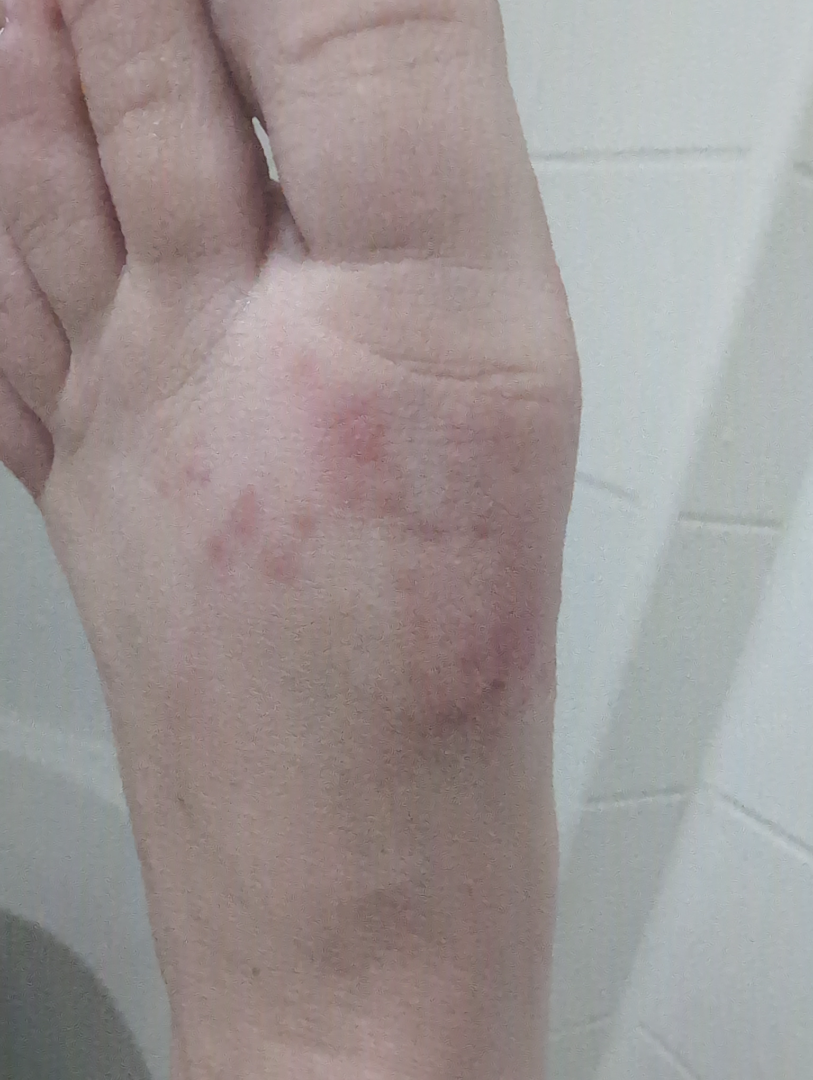Eczema (leading).